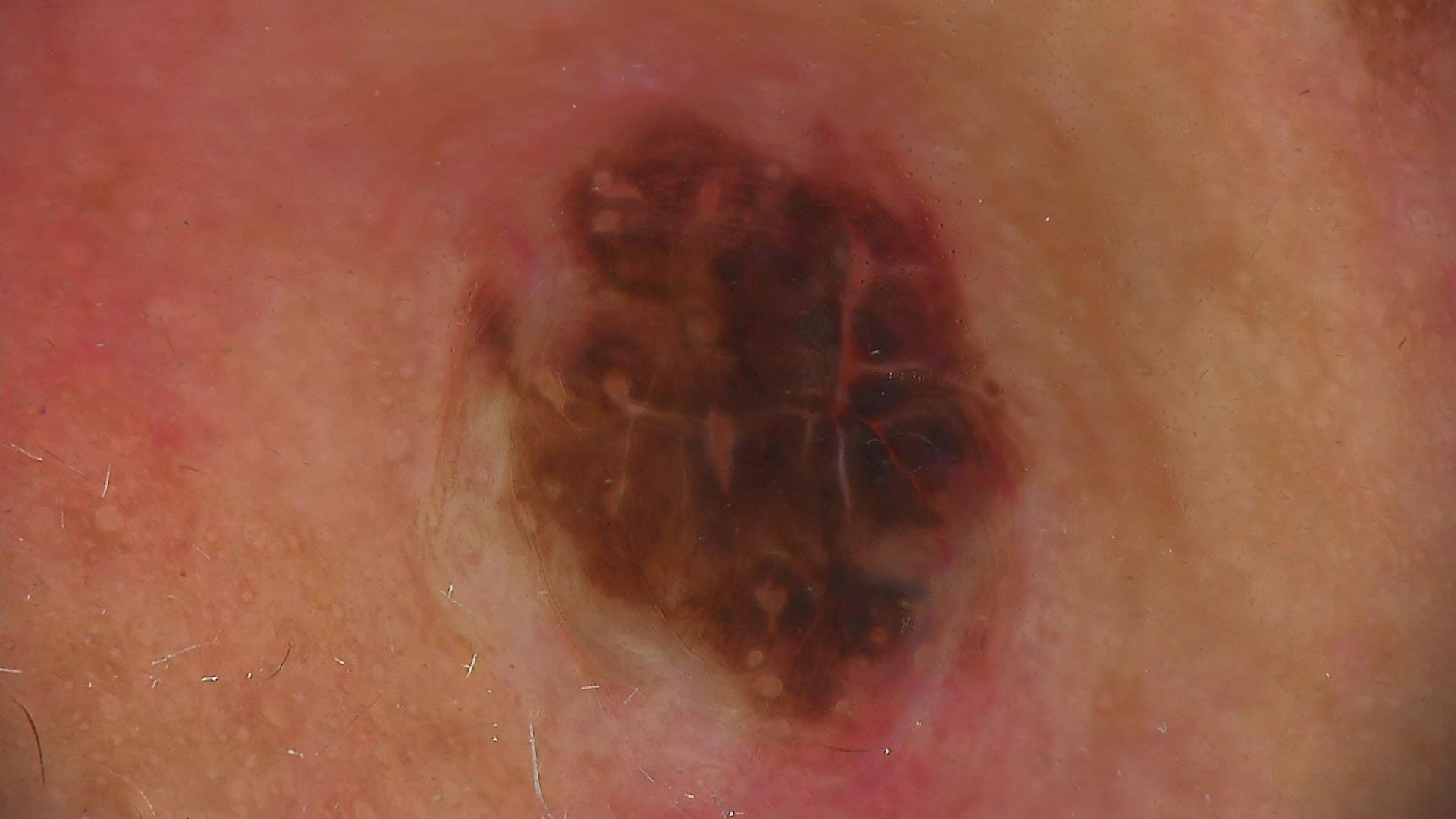Findings: A dermoscopic photograph of a skin lesion. The architecture is that of a banal lesion. Impression: Consistent with a compound nevus.